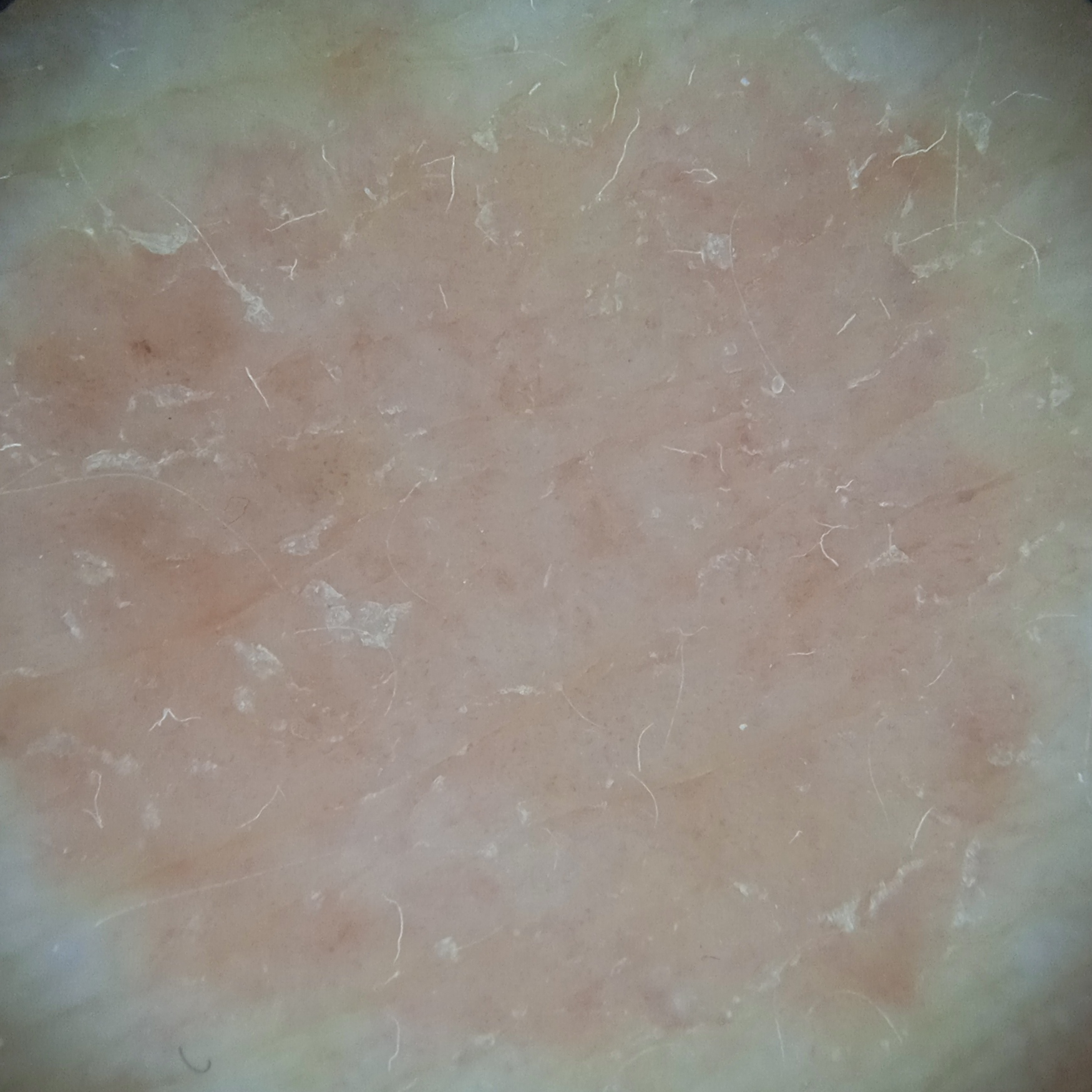A skin lesion imaged with a dermatoscope. Measuring roughly 13.2 mm. The consensus diagnosis for this lesion was a basal cell carcinoma.